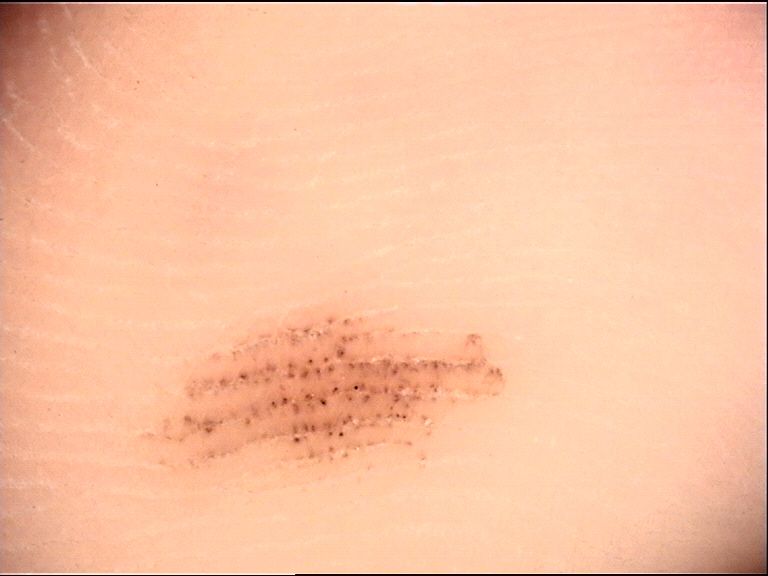The diagnostic label was an acral junctional nevus.